The affected area is the leg. The contributor reports itching. The photograph was taken at an angle. The subject is female. The lesion is described as rough or flaky.
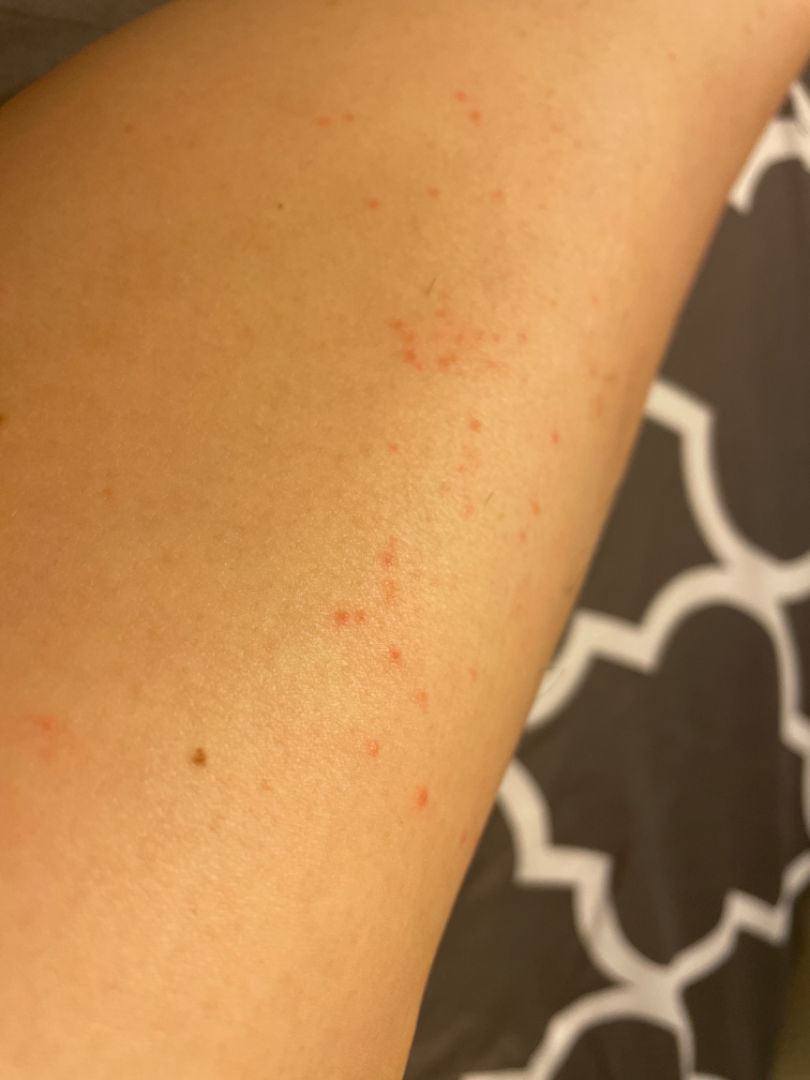On dermatologist assessment of the image: most consistent with Folliculitis.